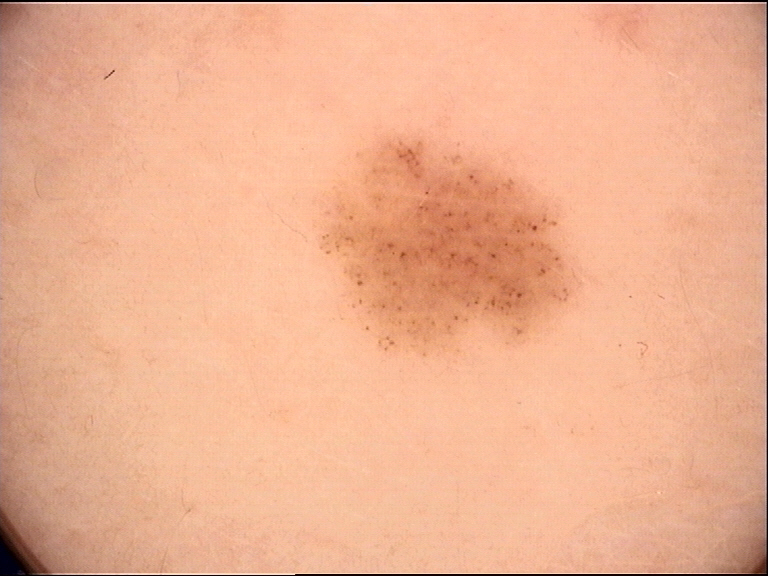label: dysplastic junctional nevus (expert consensus).